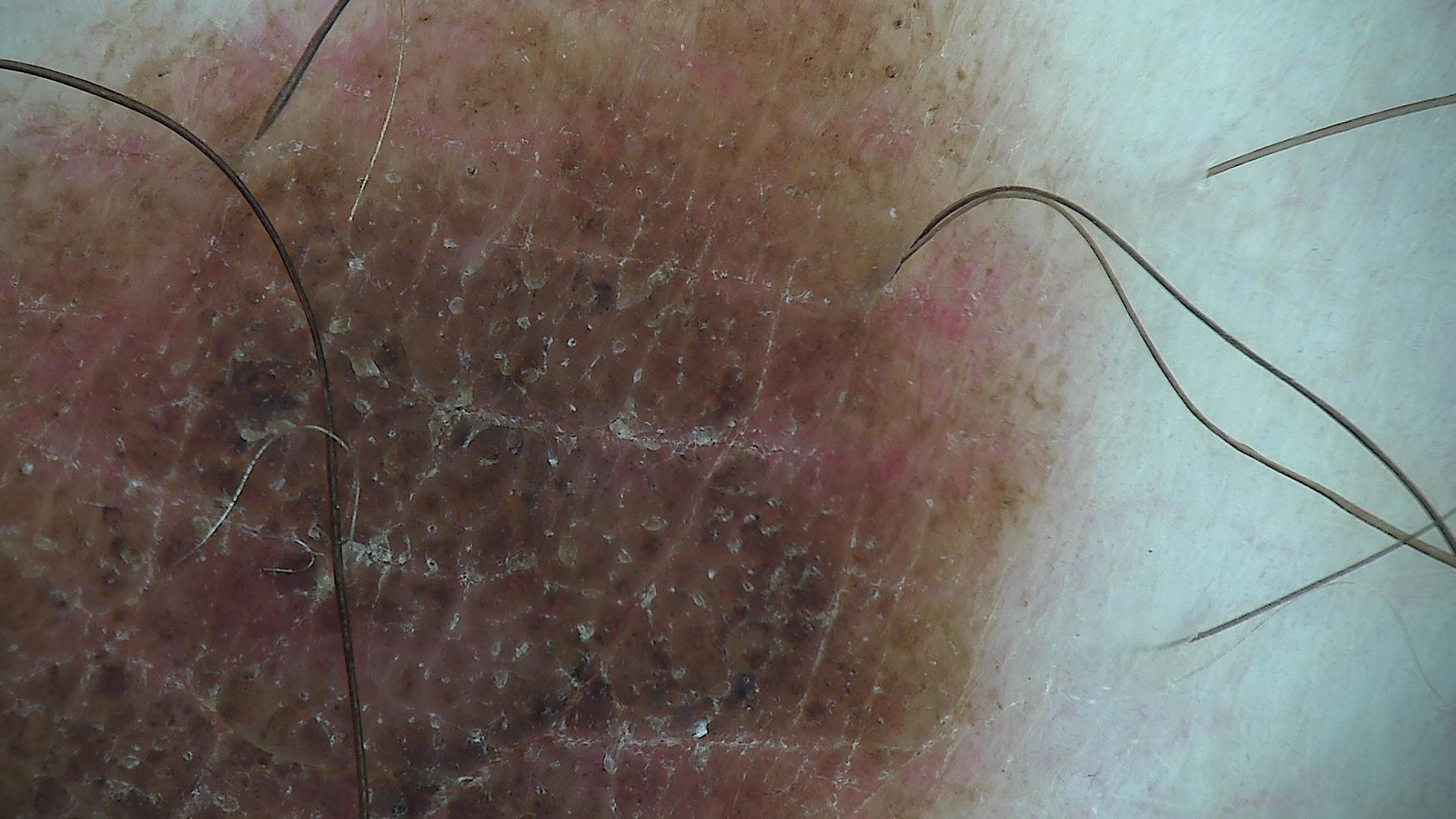{"lesion_type": {"main_class": "banal", "pattern": "compound"}, "diagnosis": {"name": "congenital compound nevus", "code": "ccb", "malignancy": "benign", "super_class": "melanocytic", "confirmation": "expert consensus"}}